A dermoscopic close-up of a skin lesion:
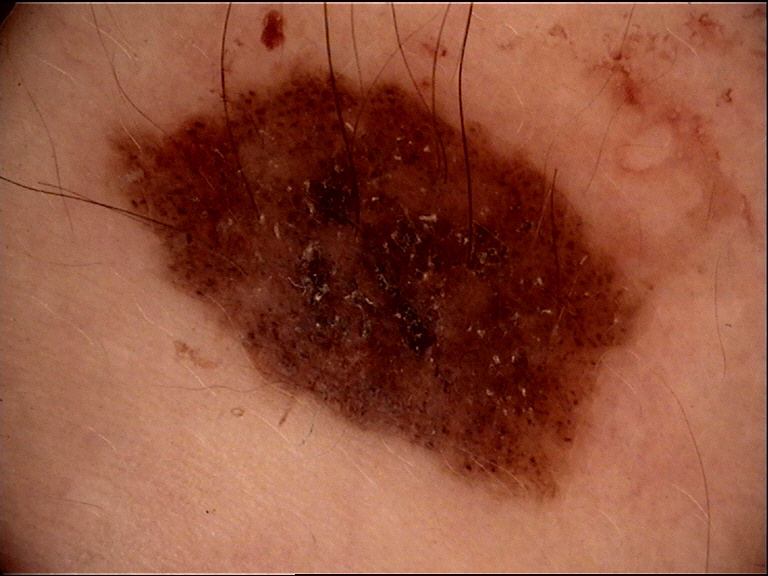Classified as a banal lesion — a congenital compound nevus.